A dermoscopic photograph of a skin lesion: 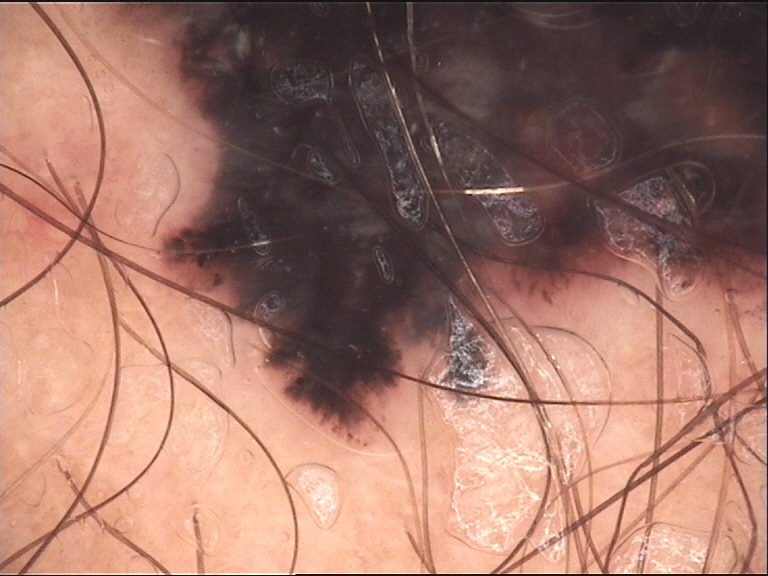Biopsy-confirmed as a skin cancer — a melanoma.